A patient age 53; a clinical photograph of a skin lesion: 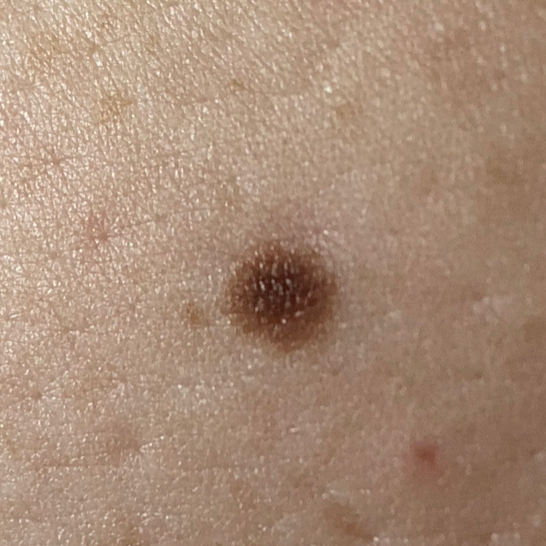Q: Where on the body is the lesion?
A: the abdomen
Q: What does the patient describe?
A: none reported
Q: What is this lesion?
A: nevus (clinical consensus)